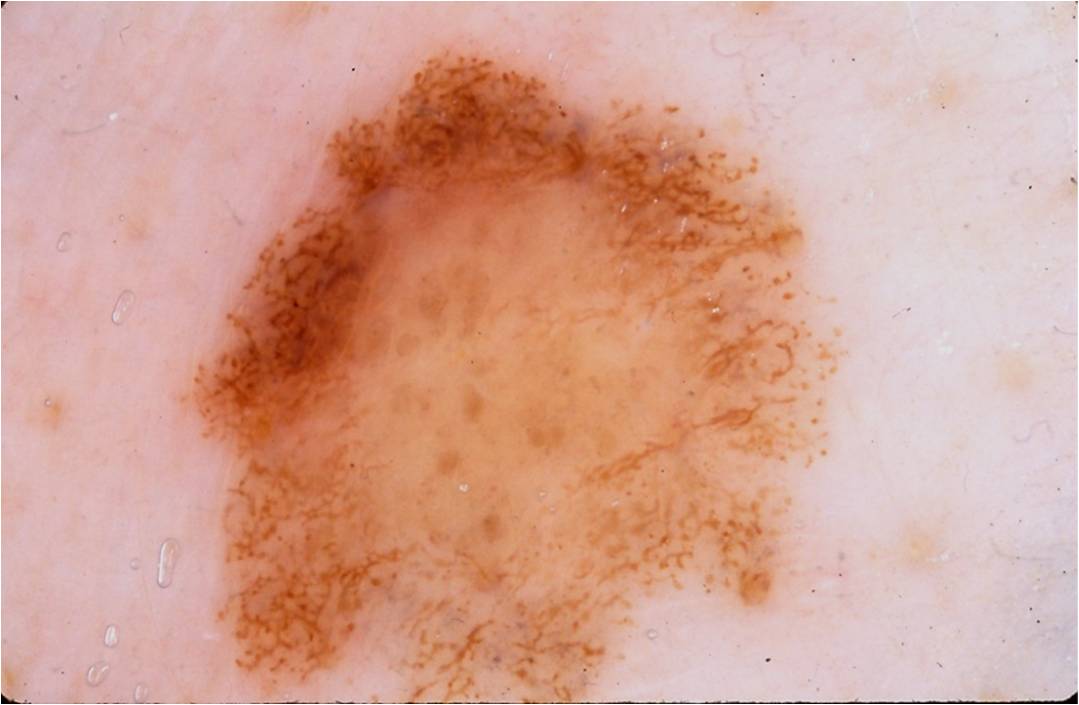Findings: A skin lesion imaged with a dermatoscope. The lesion is bounded by left=170, top=37, right=853, bottom=702. A large lesion occupying much of the field. Conclusion: Expert review diagnosed this as a benign lesion.